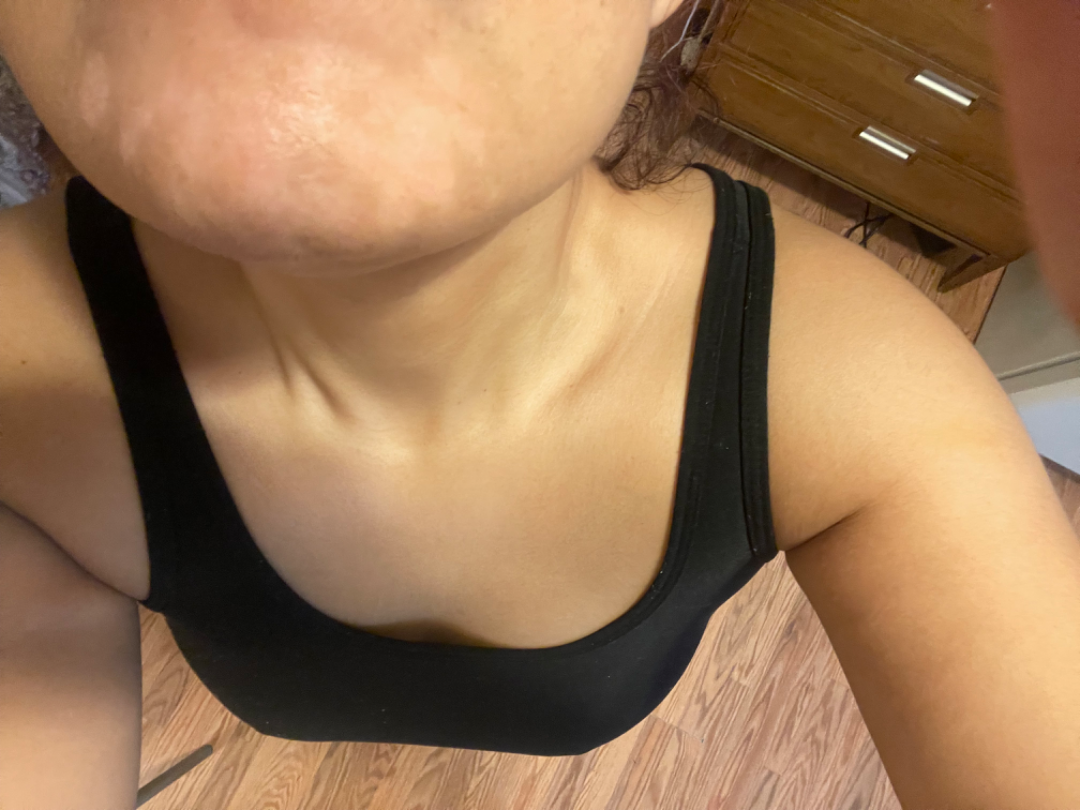assessment: not assessable
shot type: close-up
affected area: arm